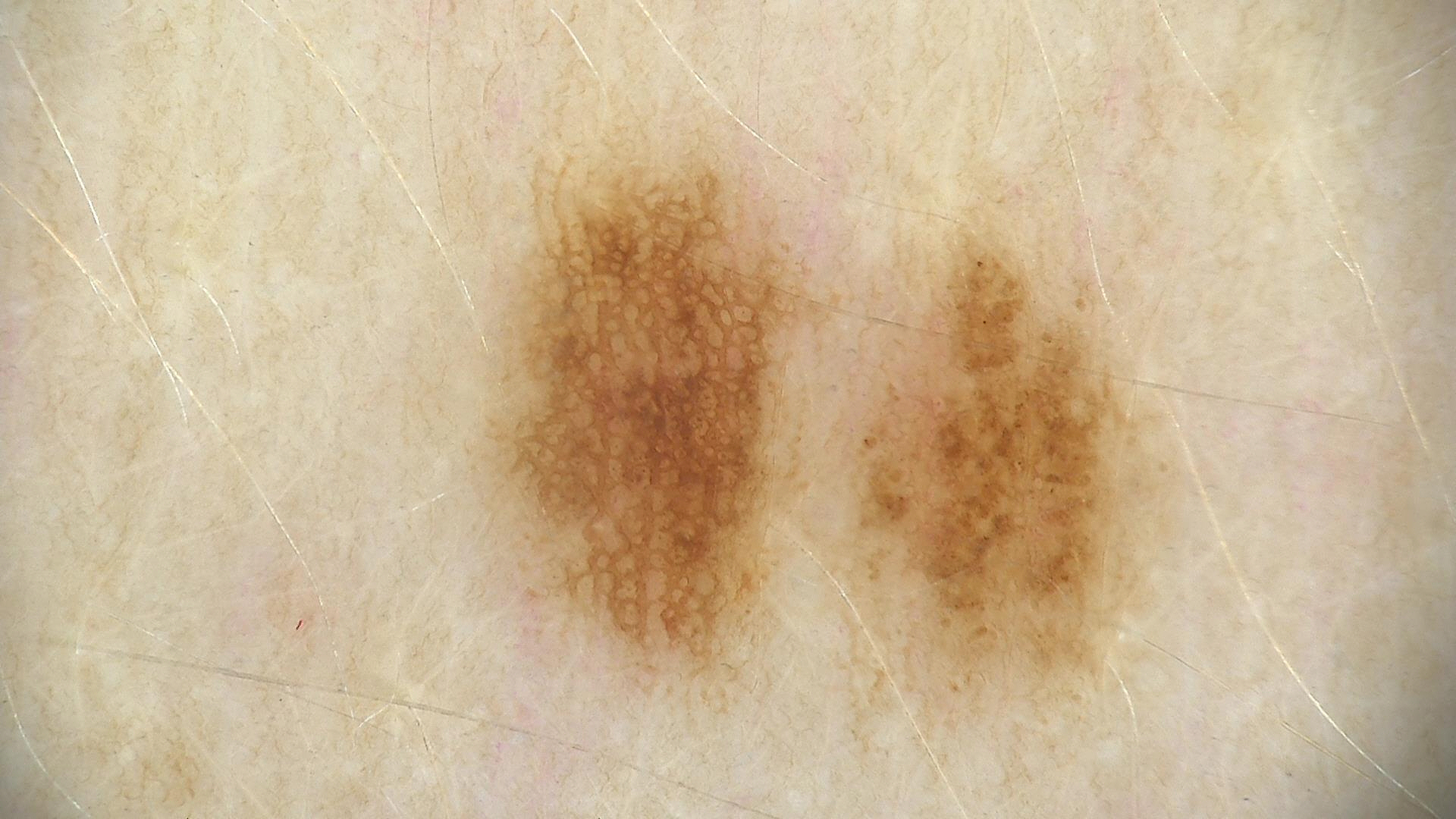image = dermoscopy | assessment = dysplastic junctional nevus (expert consensus).